A dermoscopic close-up of a skin lesion.
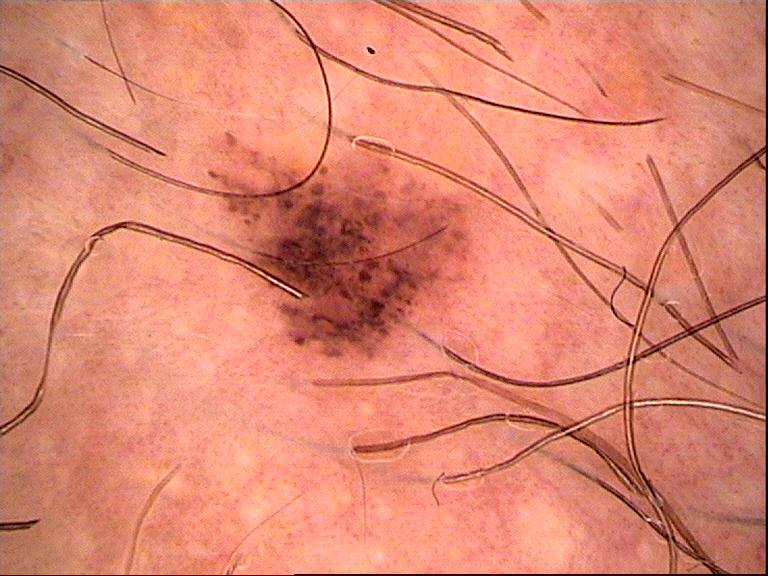Impression: The diagnosis was a dysplastic junctional nevus.